The lesion involves the leg · an image taken at an angle: 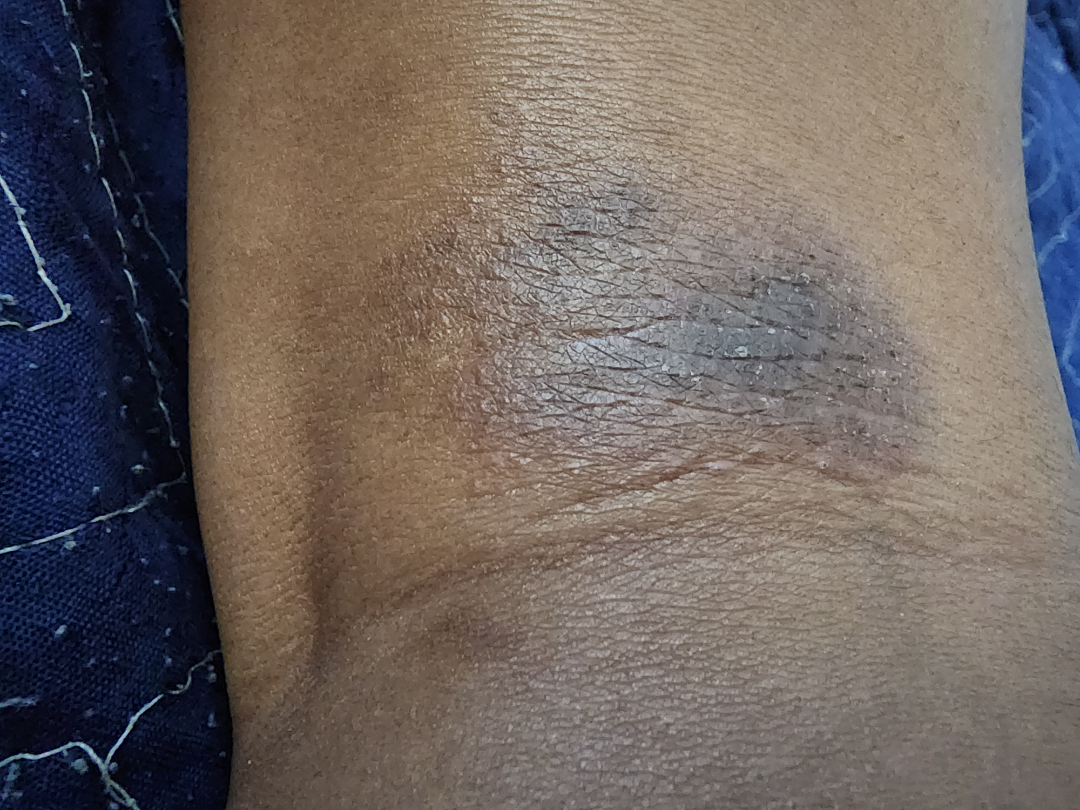Q: What is the dermatologist's impression?
A: the leading impression is Lichen Simplex Chronicus; an alternative is Lichen planus/lichenoid eruption; a remote consideration is ecchymoses